The photograph was taken at an angle. The patient is 30–39, female:
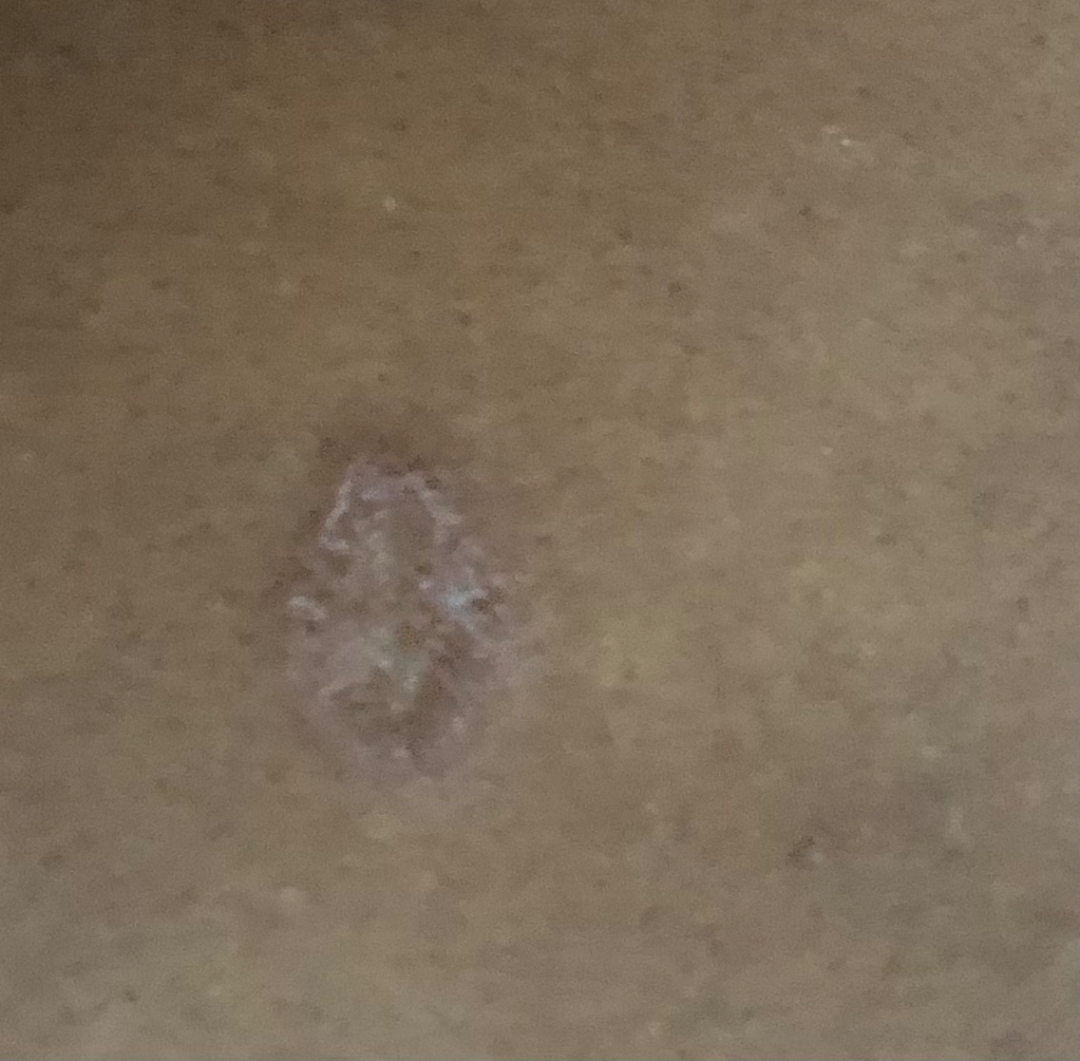Notes:
* clinical impression: the leading consideration is Tinea; possibly Deep fungal infection; an alternative is SCC/SCCIS; less likely is Tuberculosis of skin and subcutaneous tissue